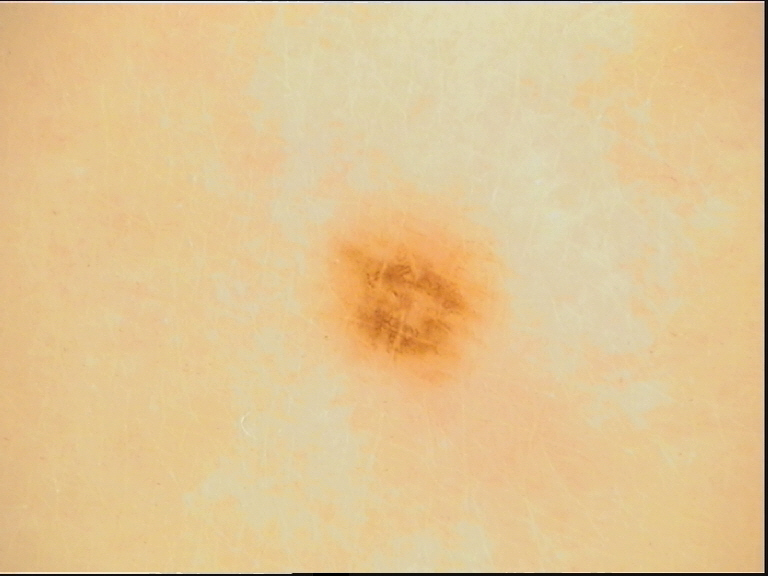Q: What is this lesion?
A: dysplastic junctional nevus (expert consensus)